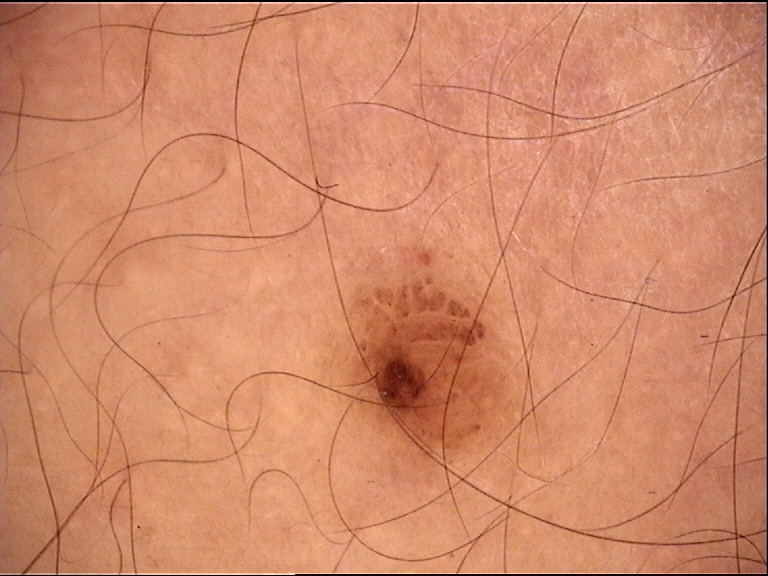{"image": "dermatoscopy", "diagnosis": {"name": "dysplastic compound nevus", "code": "cd", "malignancy": "benign", "super_class": "melanocytic", "confirmation": "expert consensus"}}